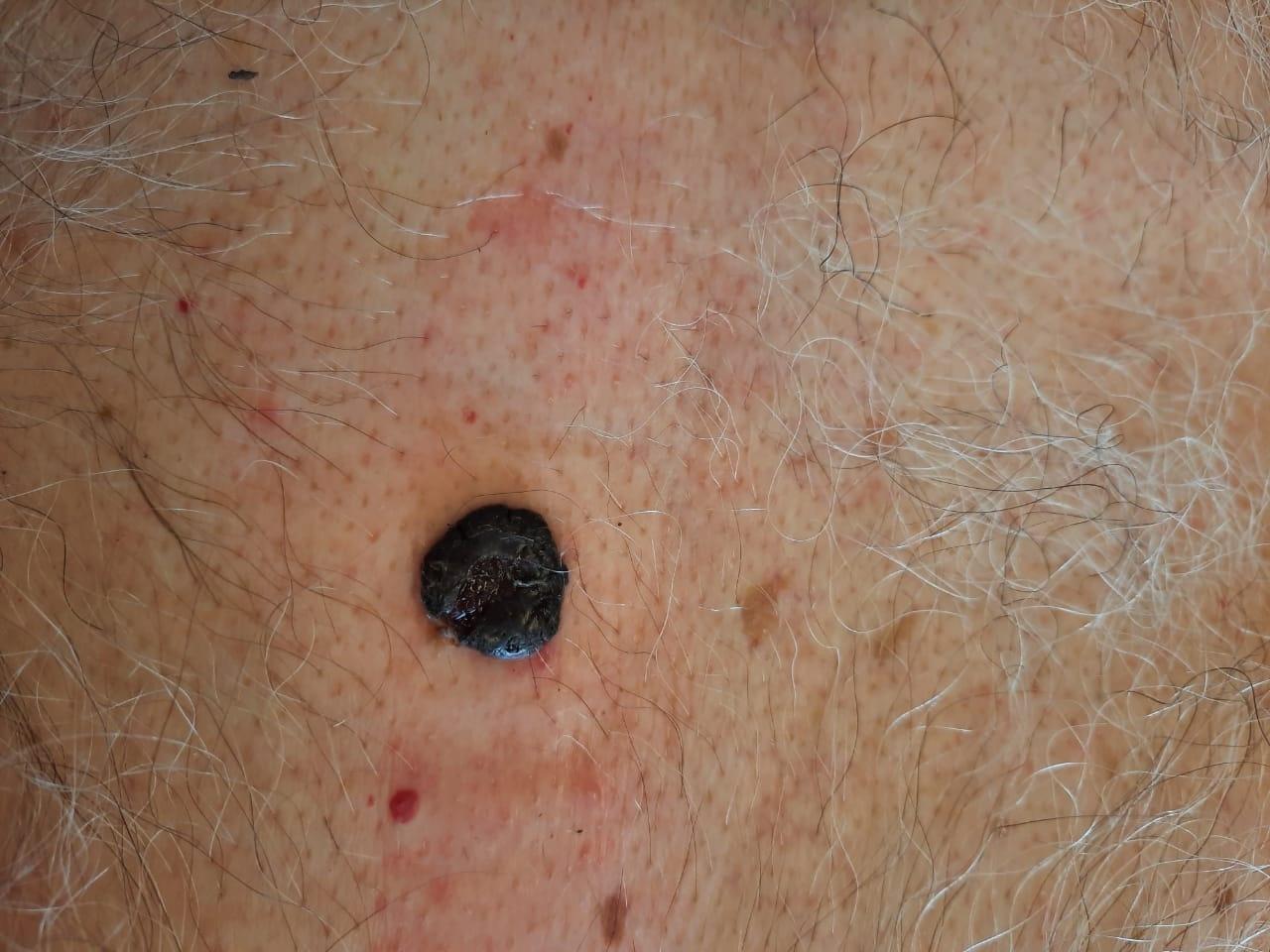The patient was assessed as Fitzpatrick phototype II. A male patient about 75 years old. A clinical photograph showing a skin lesion in context. The lesion is located on the trunk. Biopsy-confirmed as a melanoma.